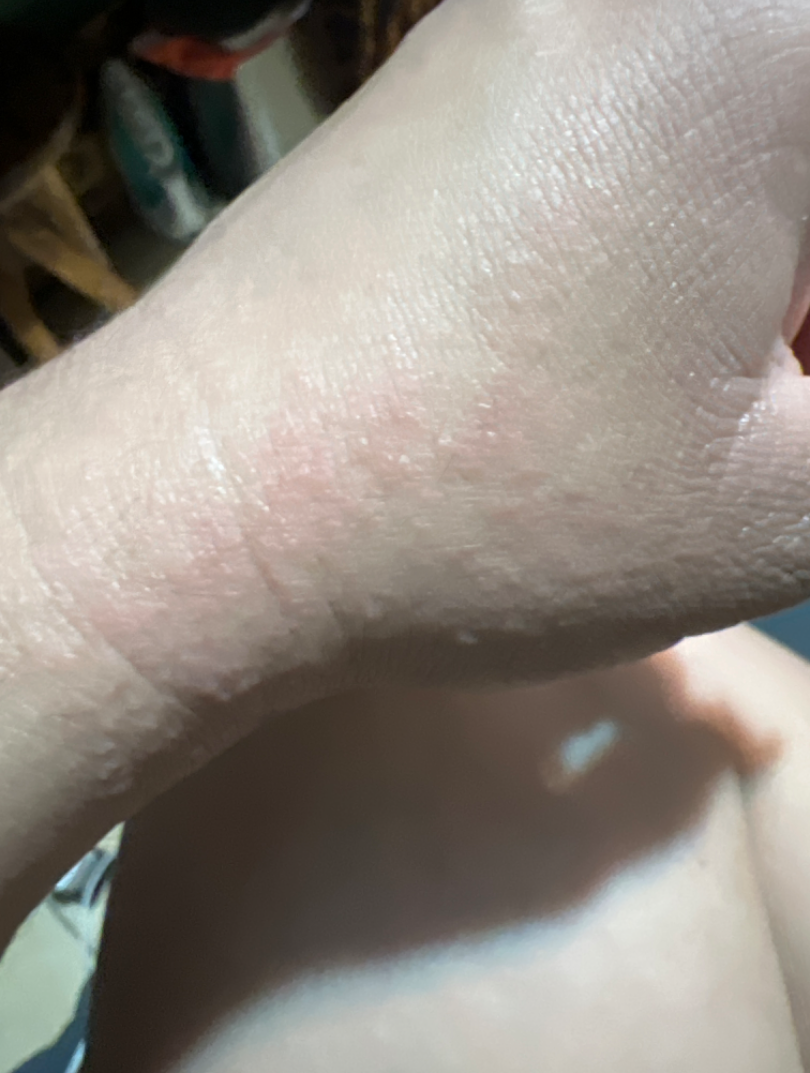Assessment:
On remote review of the image, Scabies (50%); Hypersensitivity (50%).